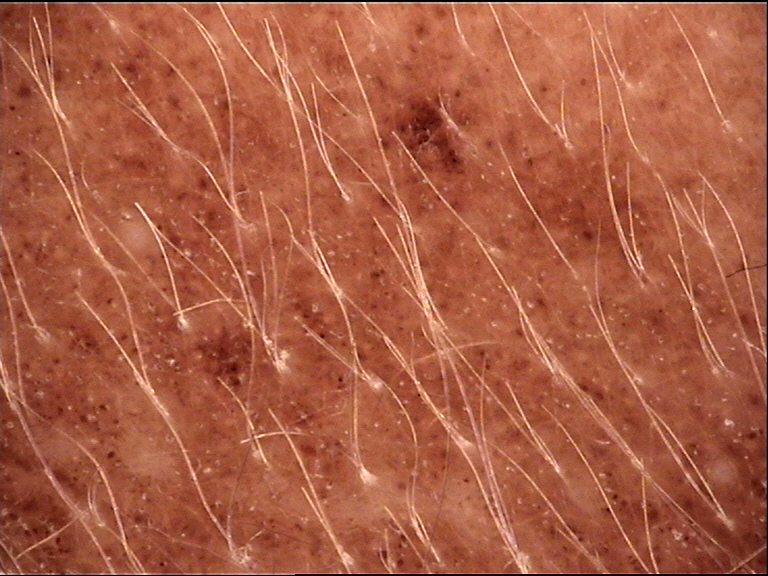image: dermatoscopy
lesion_type:
  main_class: banal
  pattern: compound
diagnosis:
  name: congenital compound nevus
  code: ccb
  malignancy: benign
  super_class: melanocytic
  confirmation: expert consensus